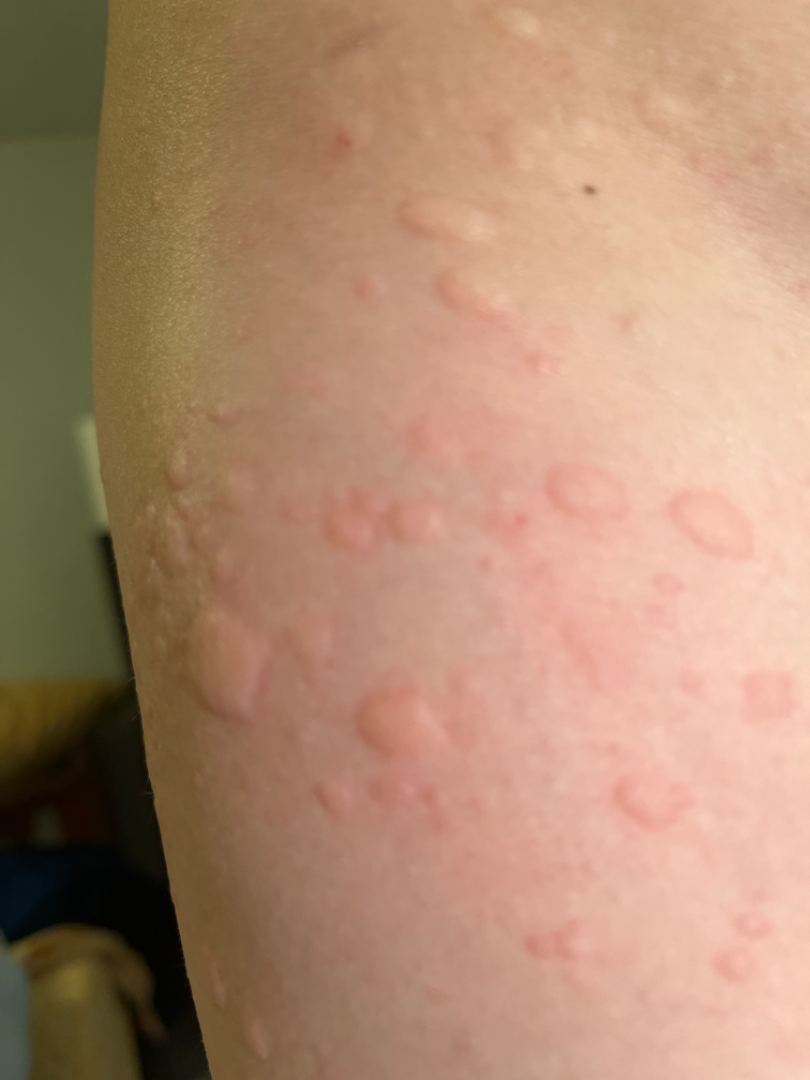The photograph was taken at an angle.
Urticaria (1.00).